Close-up view · FST I — 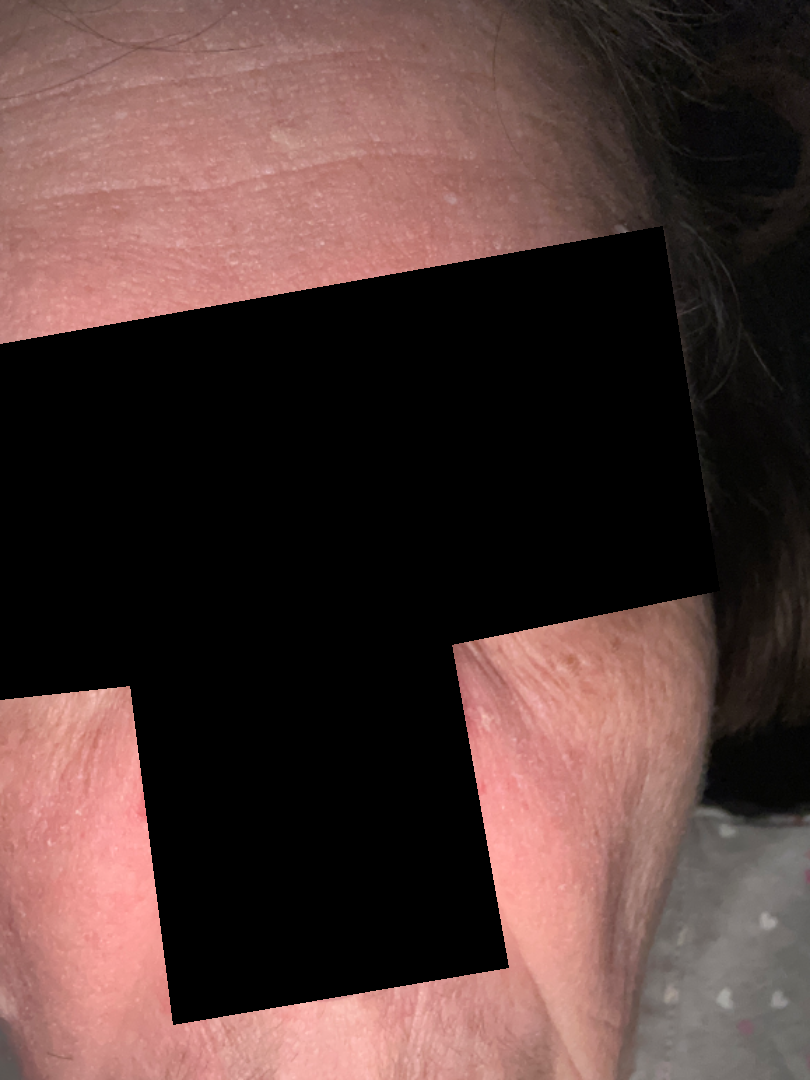clinical impression: most consistent with Seborrheic Dermatitis.